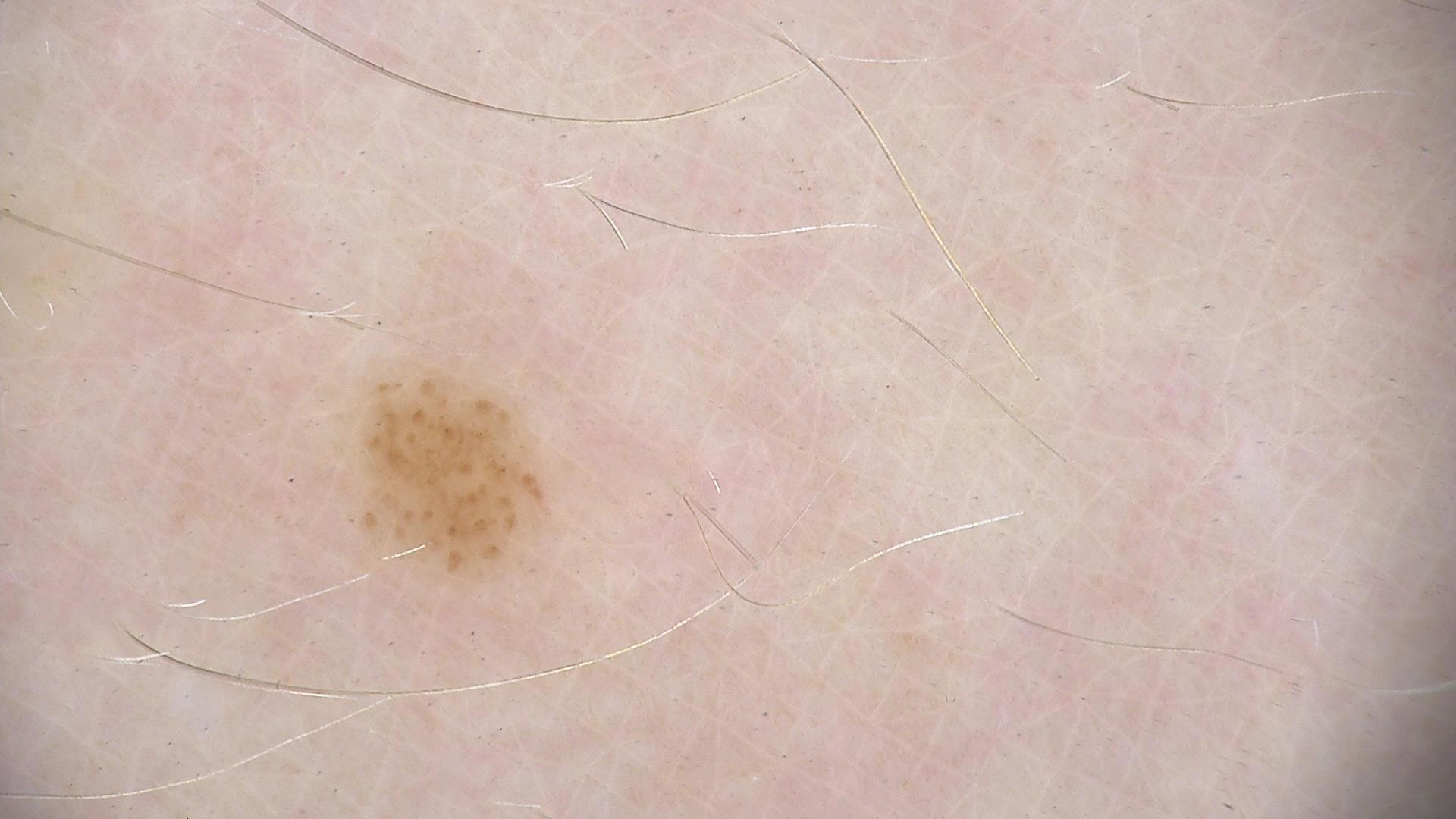class: dysplastic junctional nevus (expert consensus)